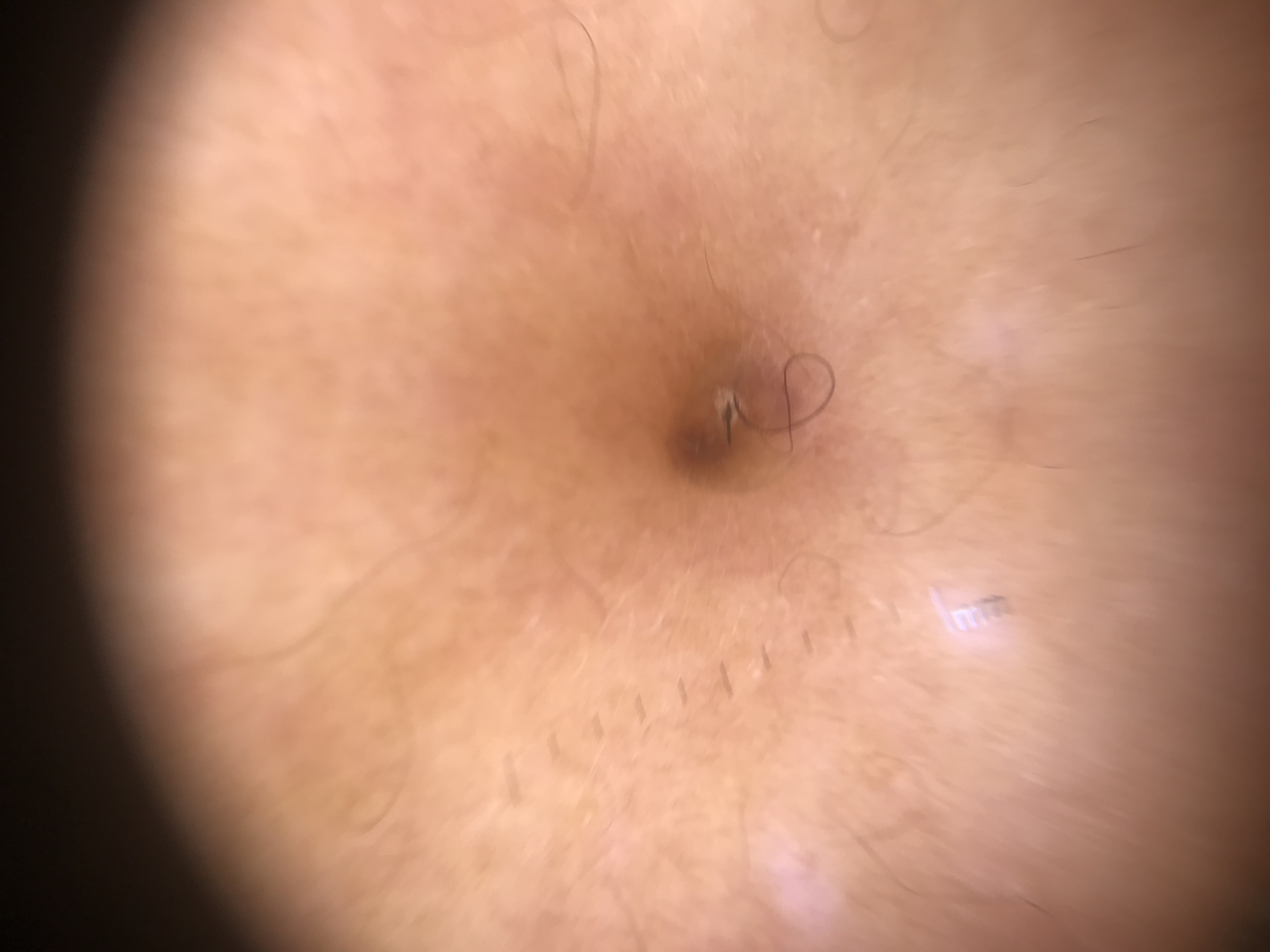Case:
A dermoscopy image of a single skin lesion. The architecture is that of a banal lesion.
Conclusion:
Classified as a dermal nevus.